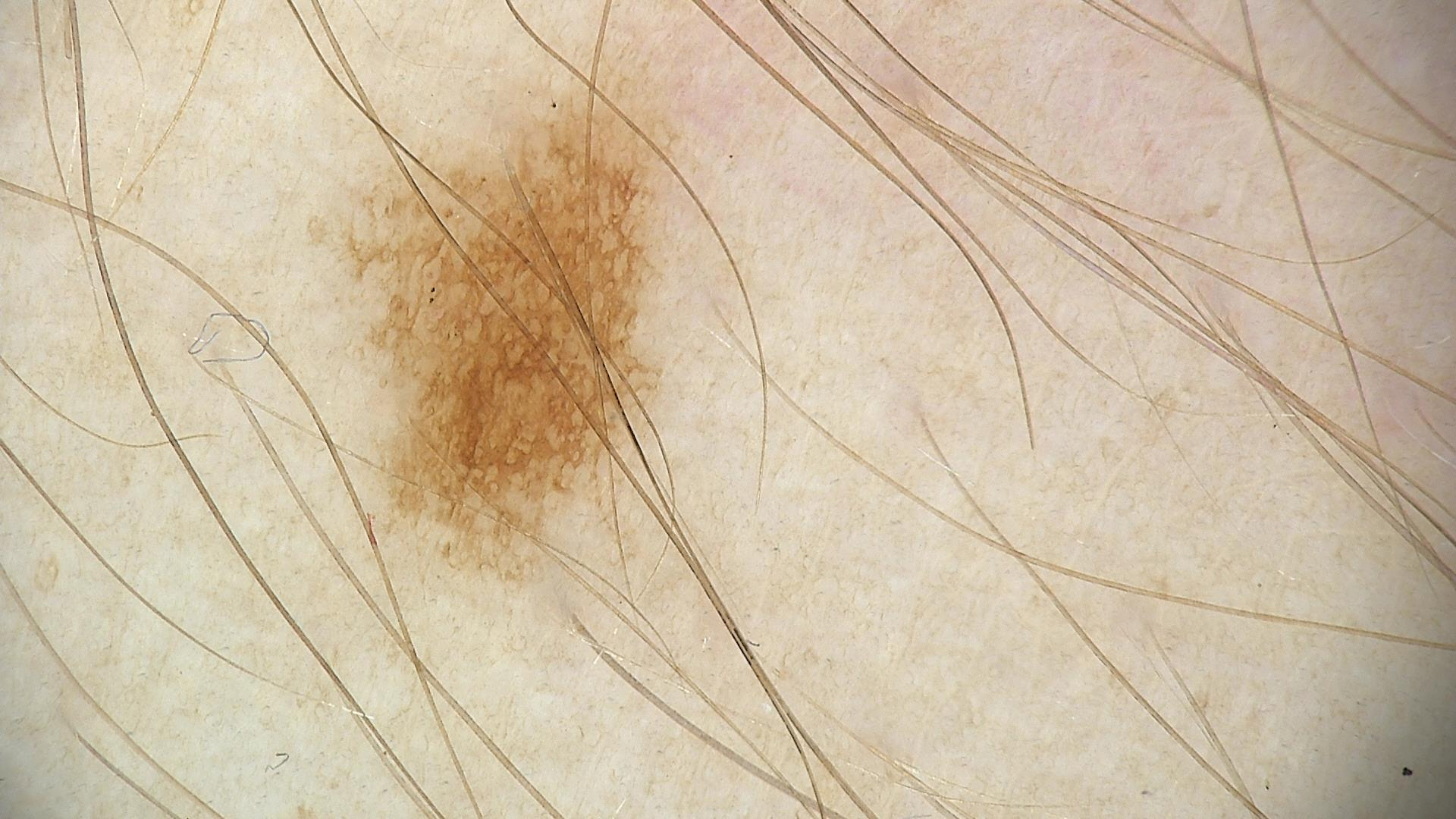diagnosis = dysplastic junctional nevus (expert consensus).